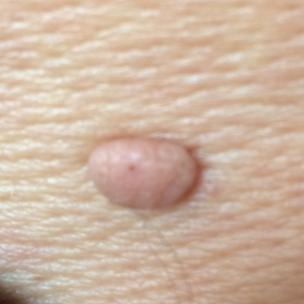The lesion is on the chest.
By the patient's account, the lesion has grown and is elevated.
The consensus clinical diagnosis was a nevus.